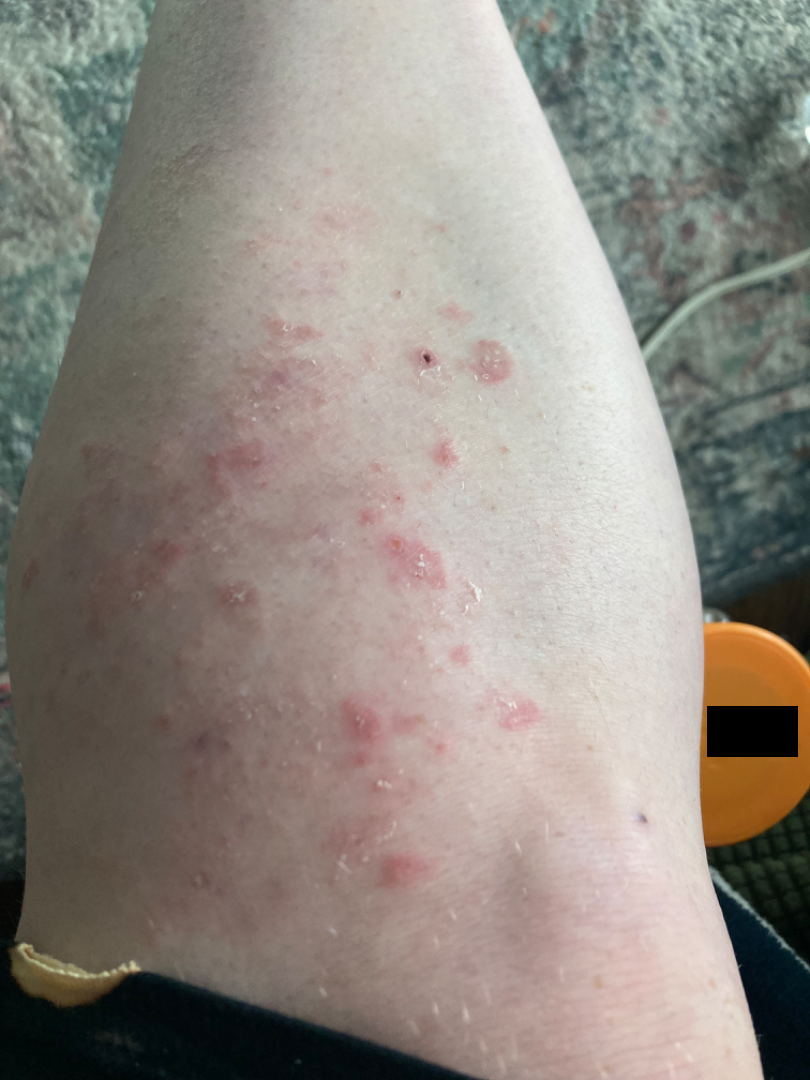present for: more than one year
site: leg
image framing: at an angle
clinical impression: Tinea (primary); Psoriasis (possible); Granuloma annulare (less likely)